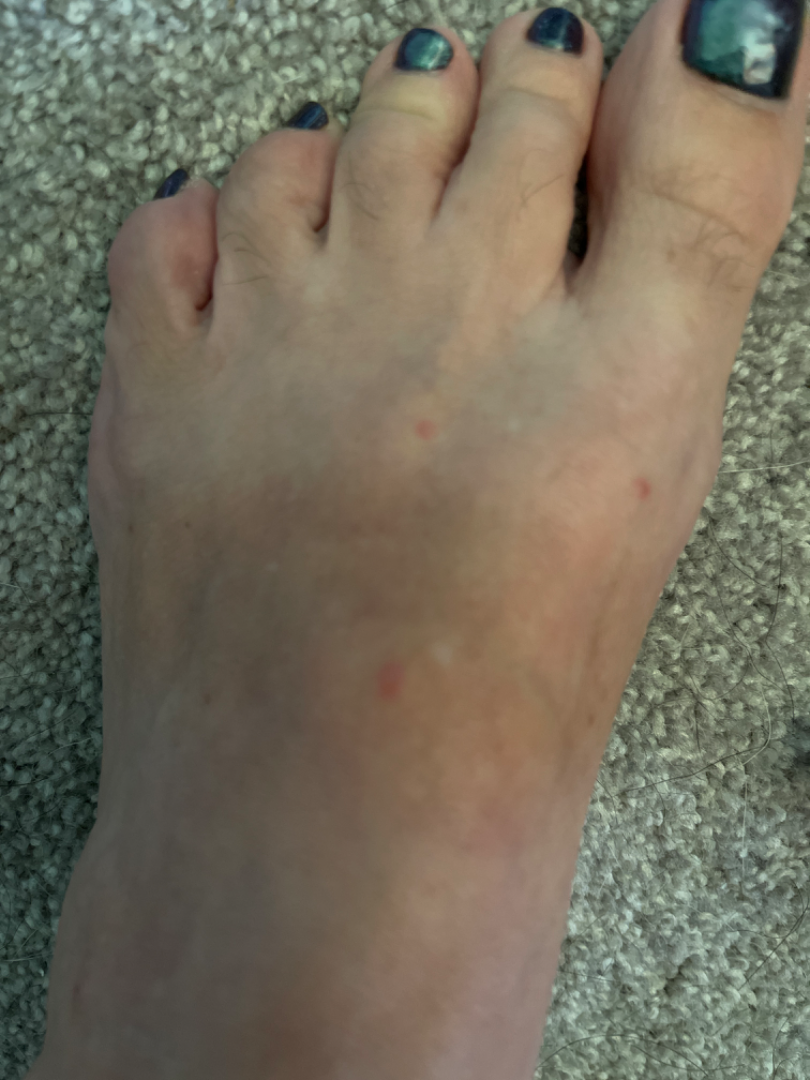The skin condition could not be confidently assessed from this image. The lesion involves the top or side of the foot. The lesion is described as raised or bumpy. This is a close-up image. Present for less than one week.